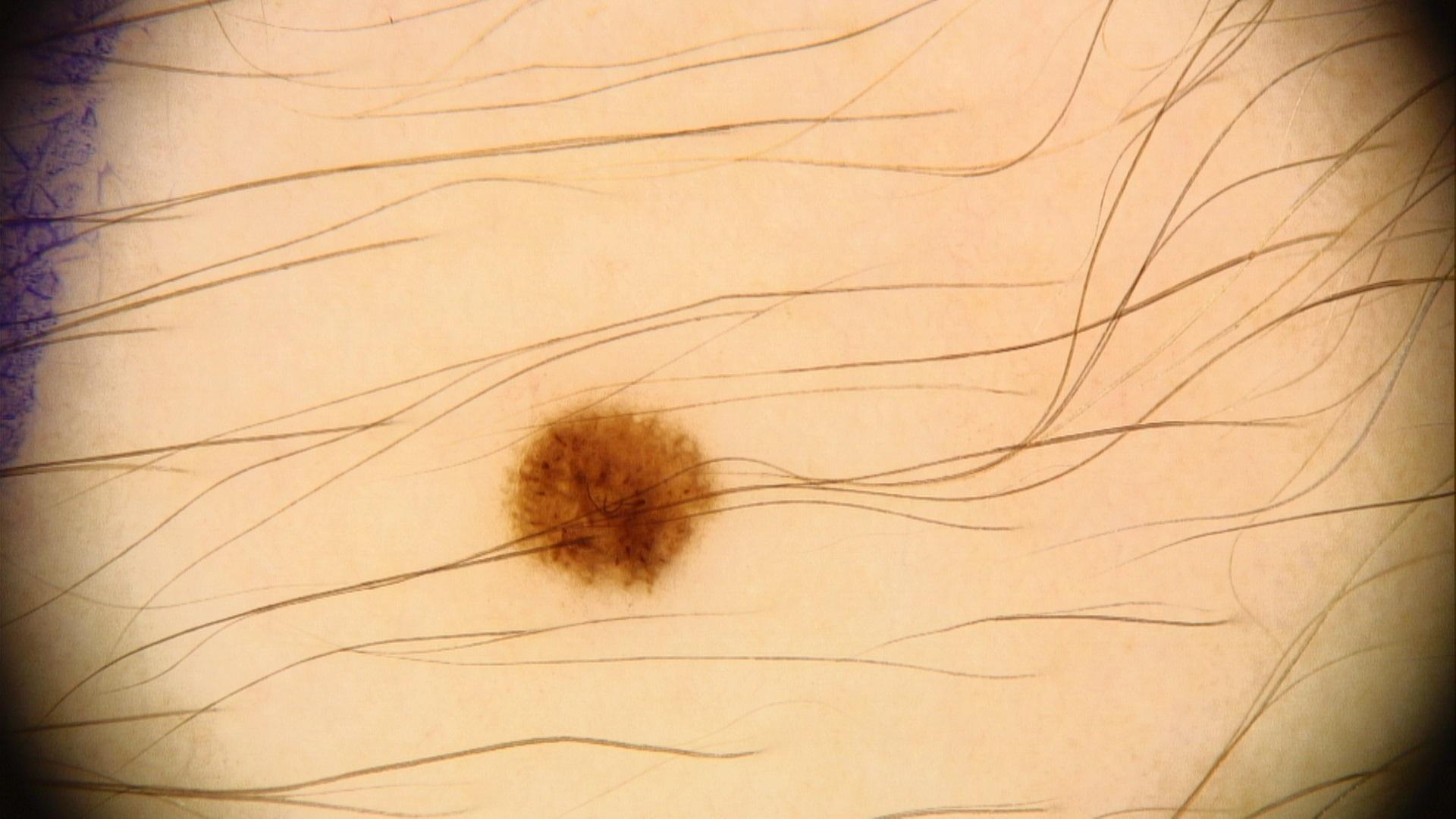The patient is FST III. A female patient aged 18 to 22. A dermoscopy image of a single skin lesion. Per the chart, melanoma in a first-degree relative but no prior melanoma. The lesion involves an upper extremity. The clinical assessment was a benign, melanocytic lesion — a nevus.